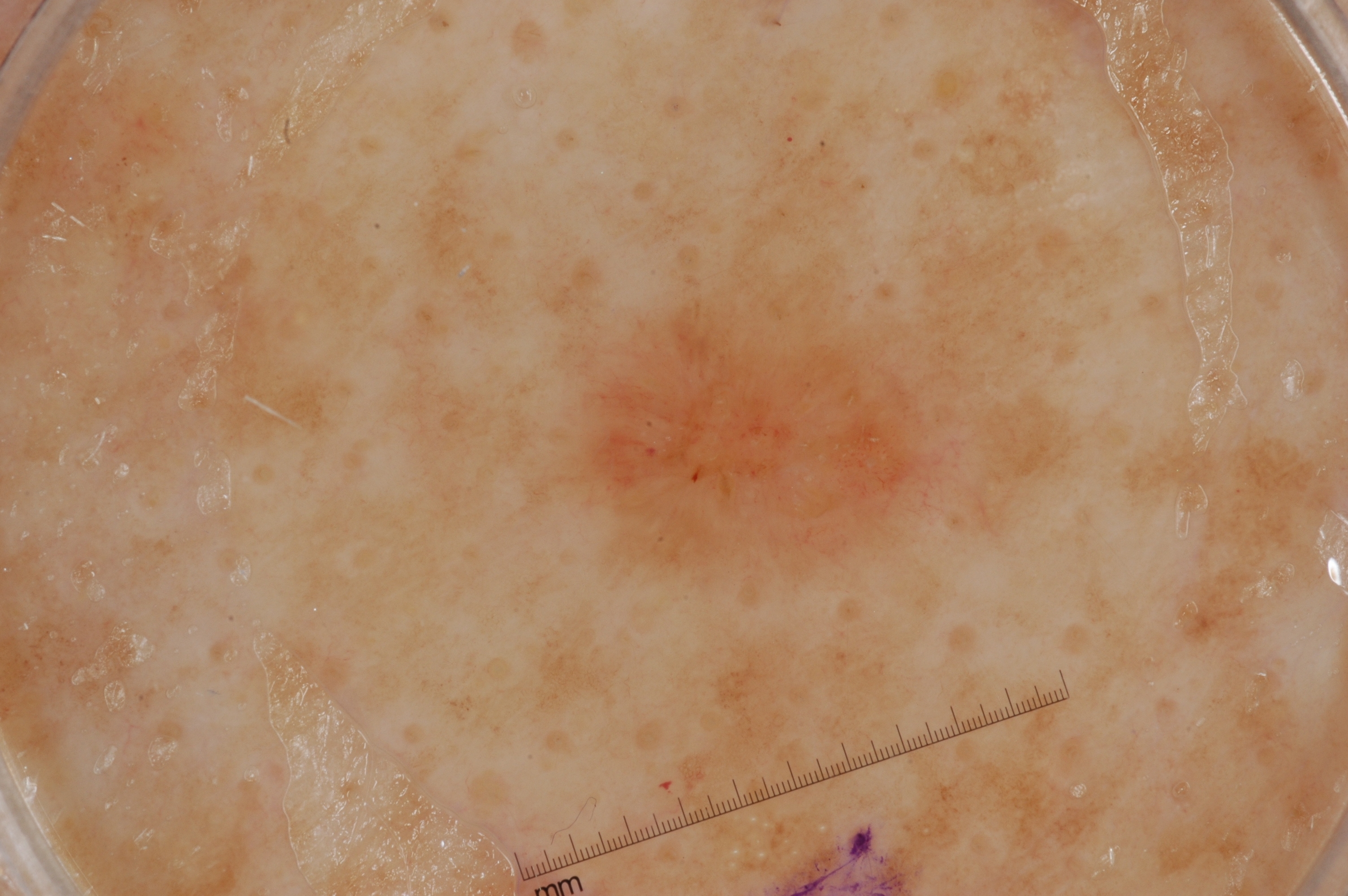Notes:
* subject · female, roughly 50 years of age
* modality · dermatoscopic image of a skin lesion
* dermoscopic features assessed but absent · negative network, milia-like cysts, pigment network, and streaks
* lesion bbox · 569, 273, 948, 581
* extent · ~7% of the field
* diagnosis · a seborrheic keratosis, a keratinocytic lesion